A dermoscopic close-up of a skin lesion.
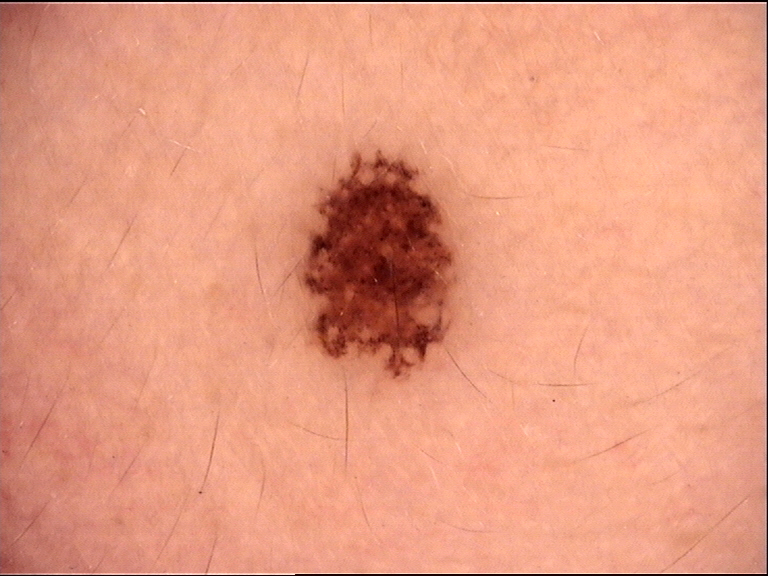Conclusion:
The diagnostic label was a benign lesion — a dysplastic junctional nevus.